A male subject aged 83 or over · contact-polarized dermoscopy of a skin lesion · the chart notes a previous melanoma: 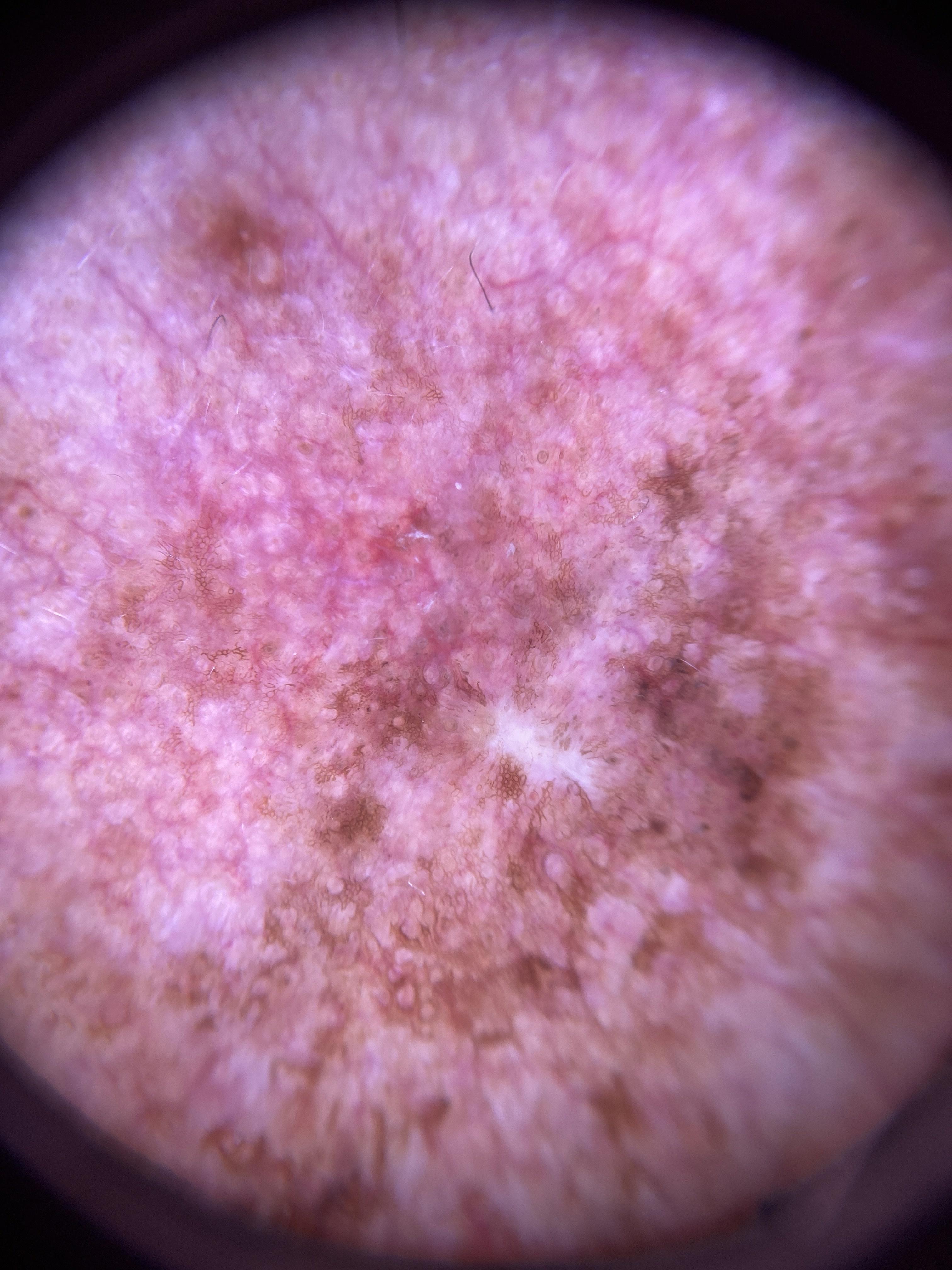Diagnosis:
Confirmed on histopathology as a malignancy — a melanoma.